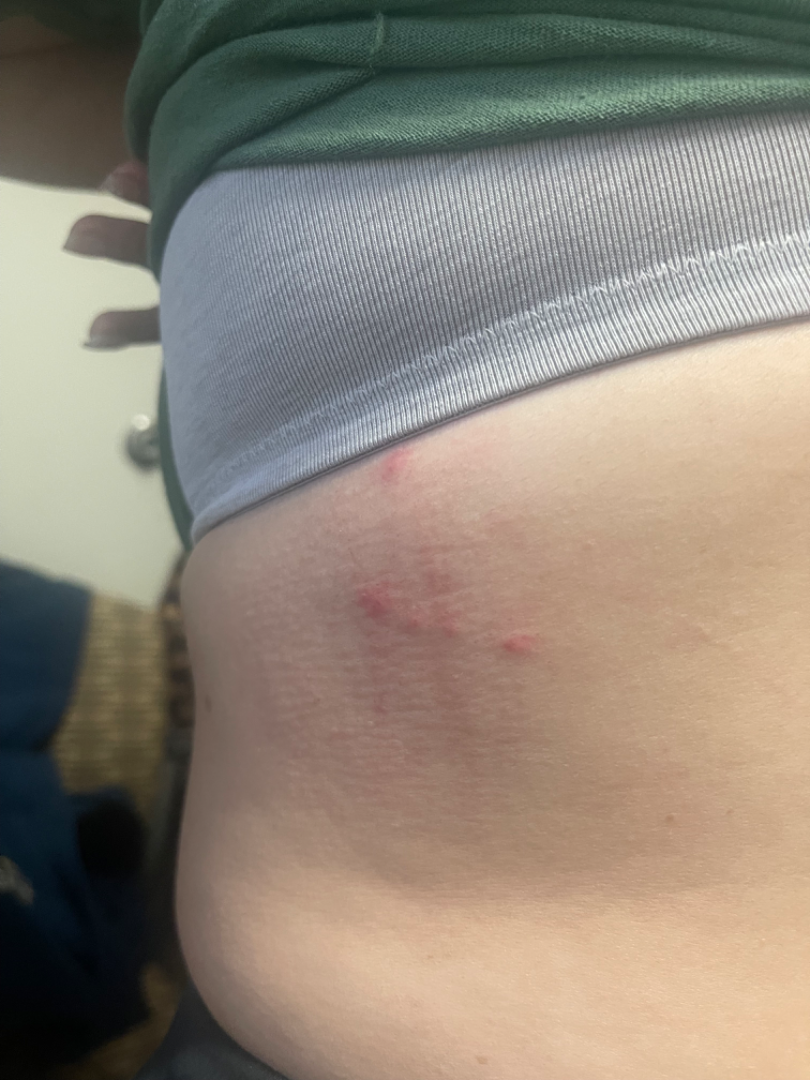assessment: ungradable on photographic review.